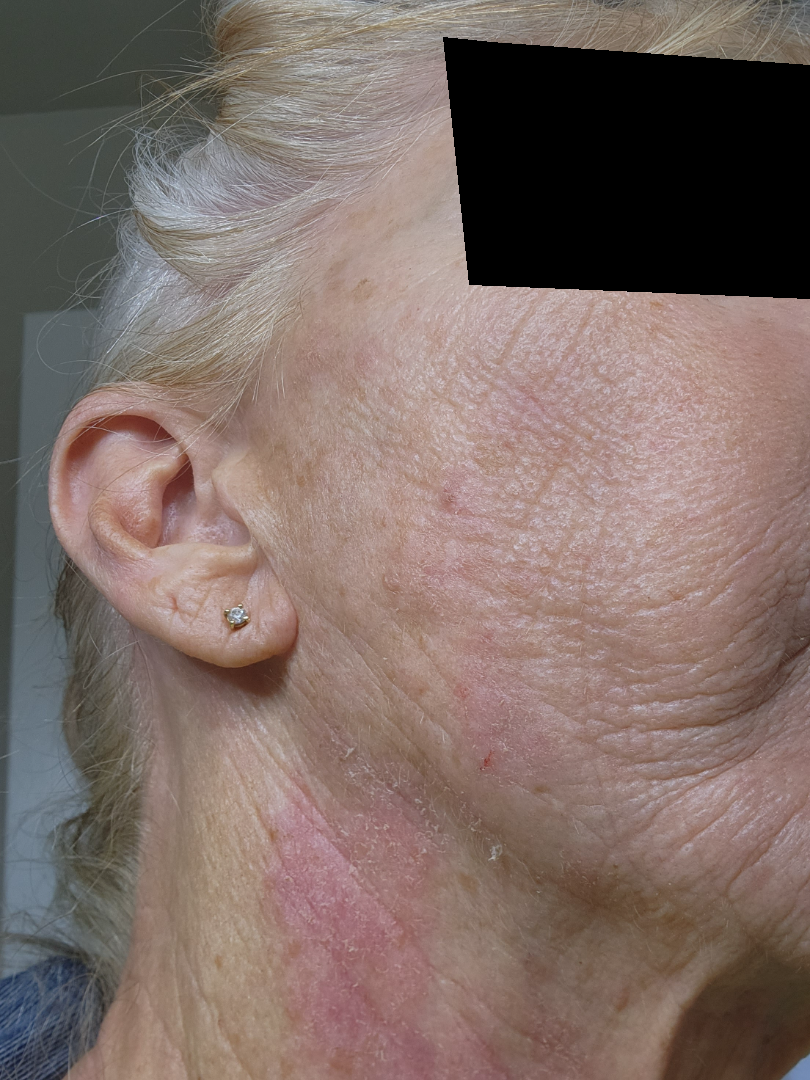| feature | finding |
|---|---|
| site | head or neck |
| reported symptoms | none reported |
| image framing | close-up |
| onset | one to four weeks |
| described texture | rough or flaky |
| patient's own categorization | a rash |
| differential | Acute and chronic dermatitis, Allergic Contact Dermatitis and Irritant Contact Dermatitis were each considered, in no particular order |